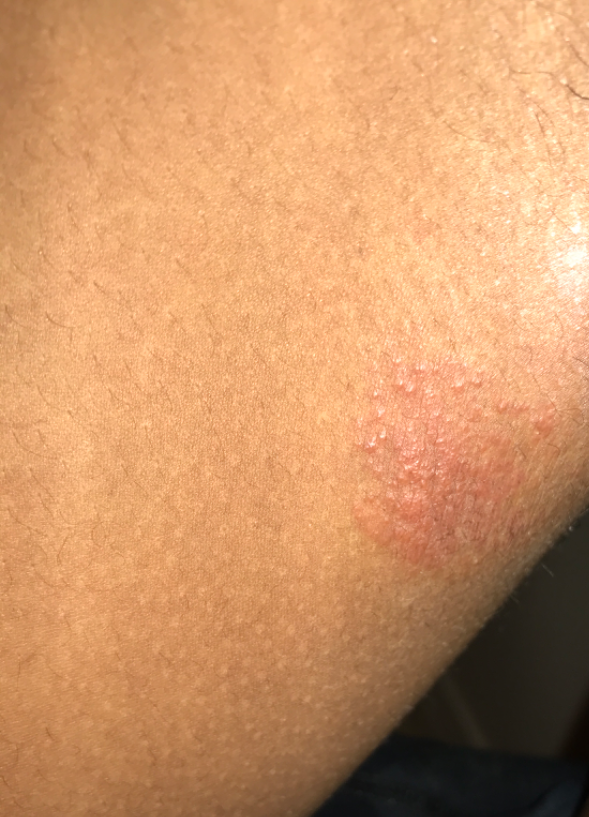This image was taken at an angle. The leg is involved. A single dermatologist reviewed the case: the differential is split between Eczema and Tinea.